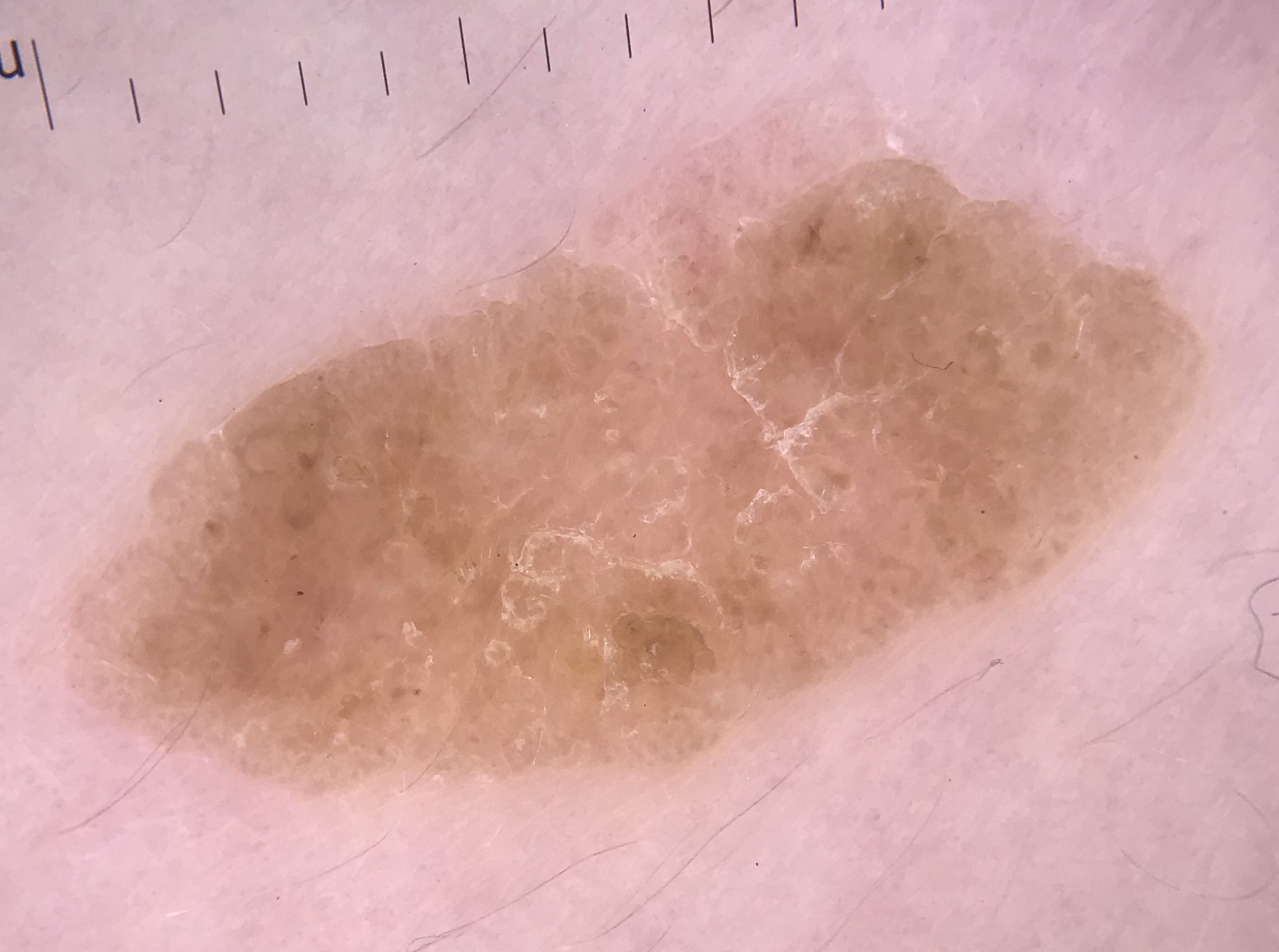Consistent with a seborrheic keratosis.